Reported duration is about one day. The photograph was taken at a distance. The patient is a female aged 70–79. Skin tone: Fitzpatrick II; lay graders estimated MST 2 (US pool) or 3 (India pool). Located on the front of the torso. Reported lesion symptoms include burning and itching. Texture is reported as raised or bumpy.
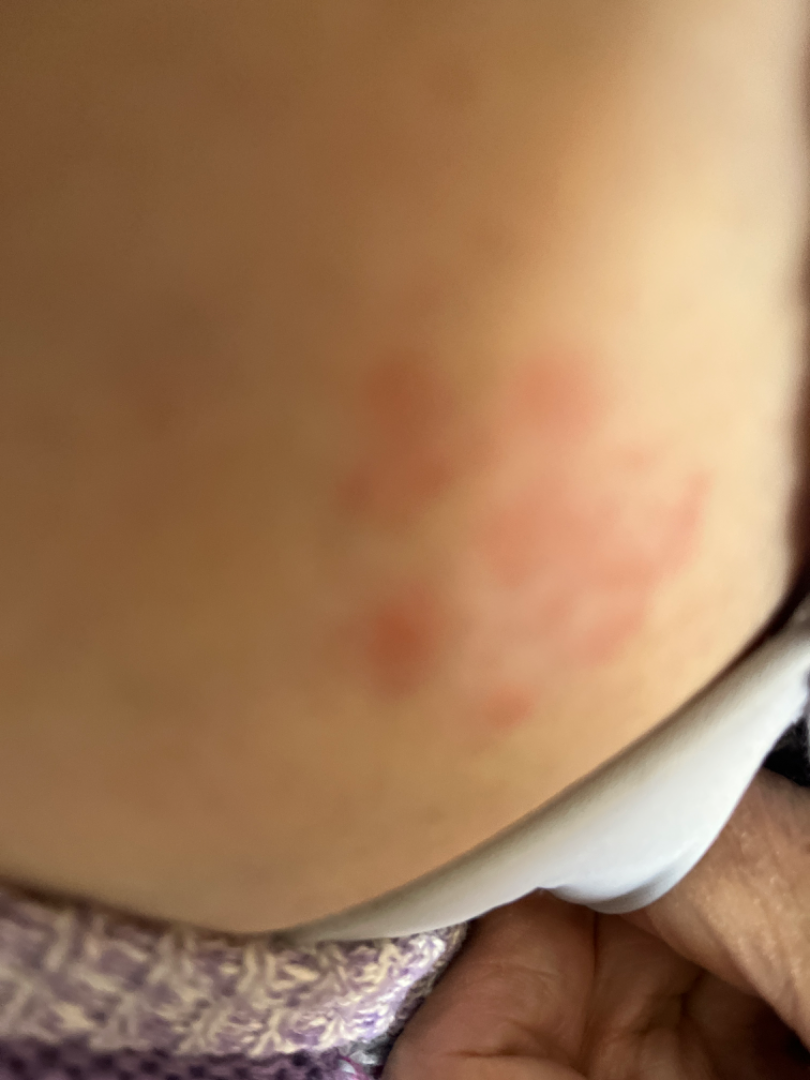Insect Bite, Allergic Contact Dermatitis and Herpes Simplex were each considered, in no particular order.